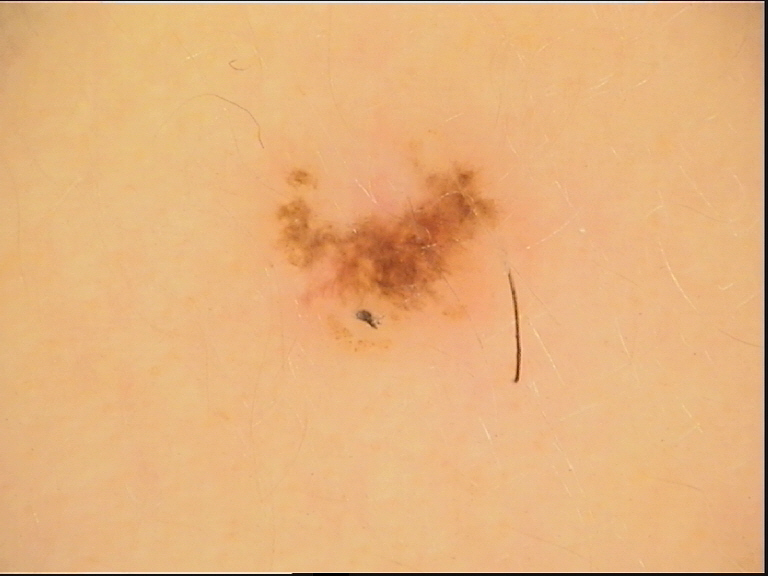Impression:
The diagnosis was a dysplastic junctional nevus.